A dermoscopy image of a single skin lesion.
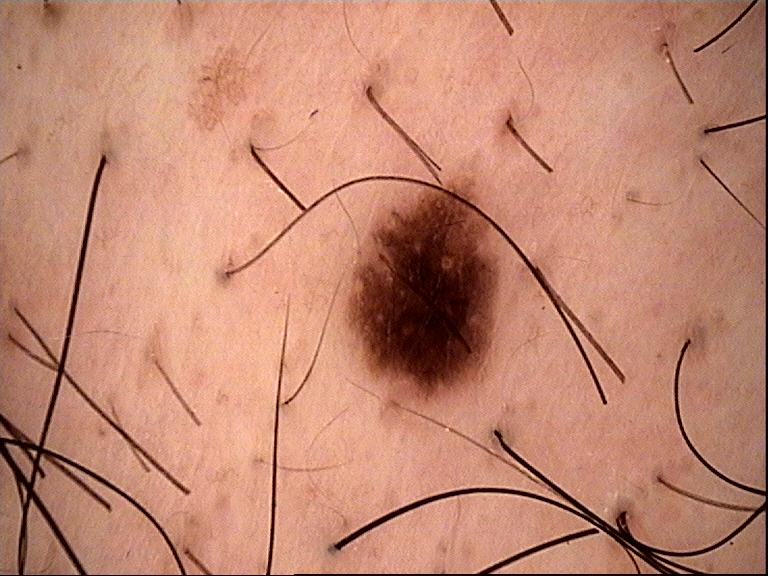- diagnostic label · dysplastic junctional nevus (expert consensus)